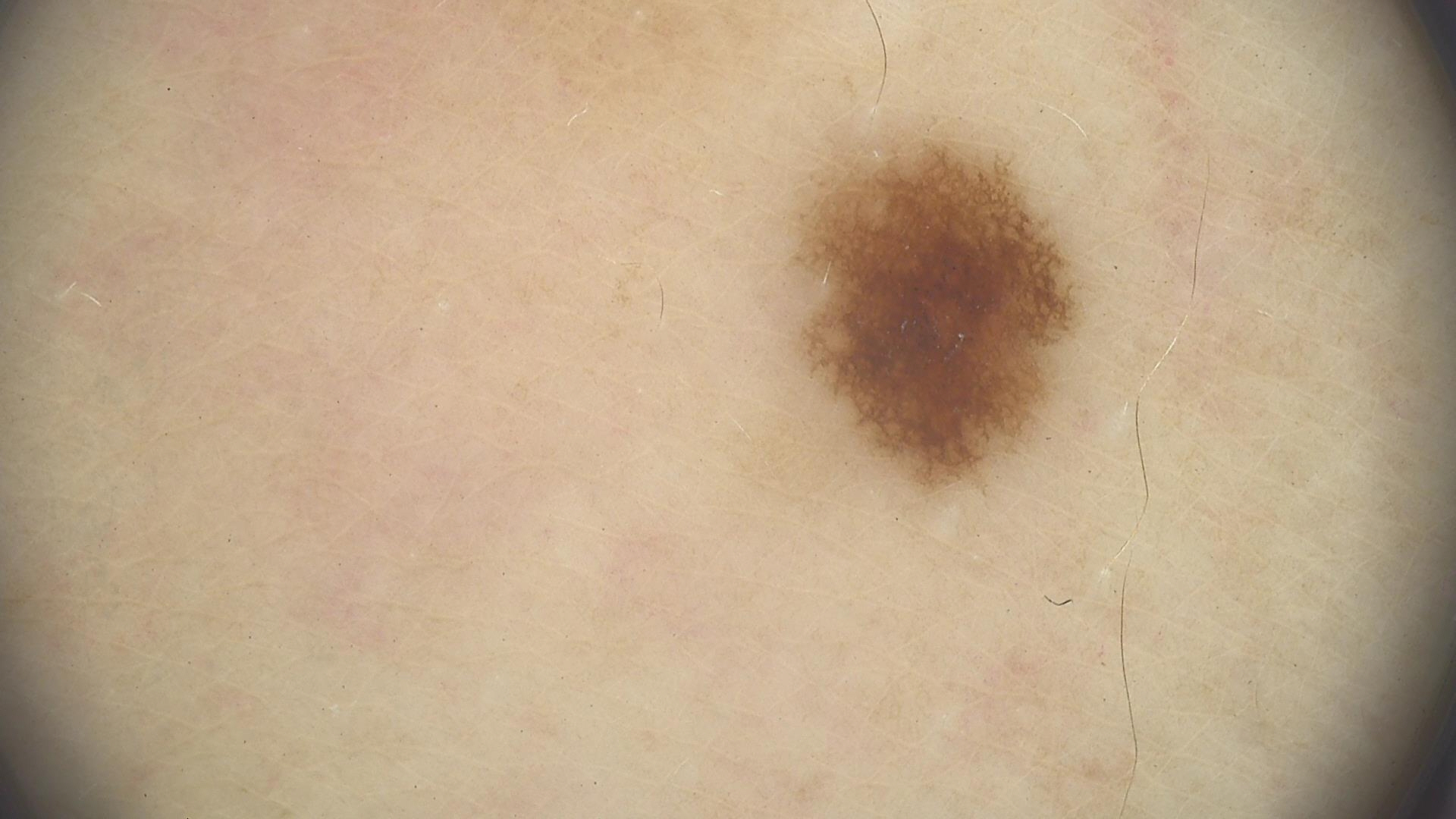Labeled as a dysplastic junctional nevus.